A dermoscopy image of a single skin lesion.
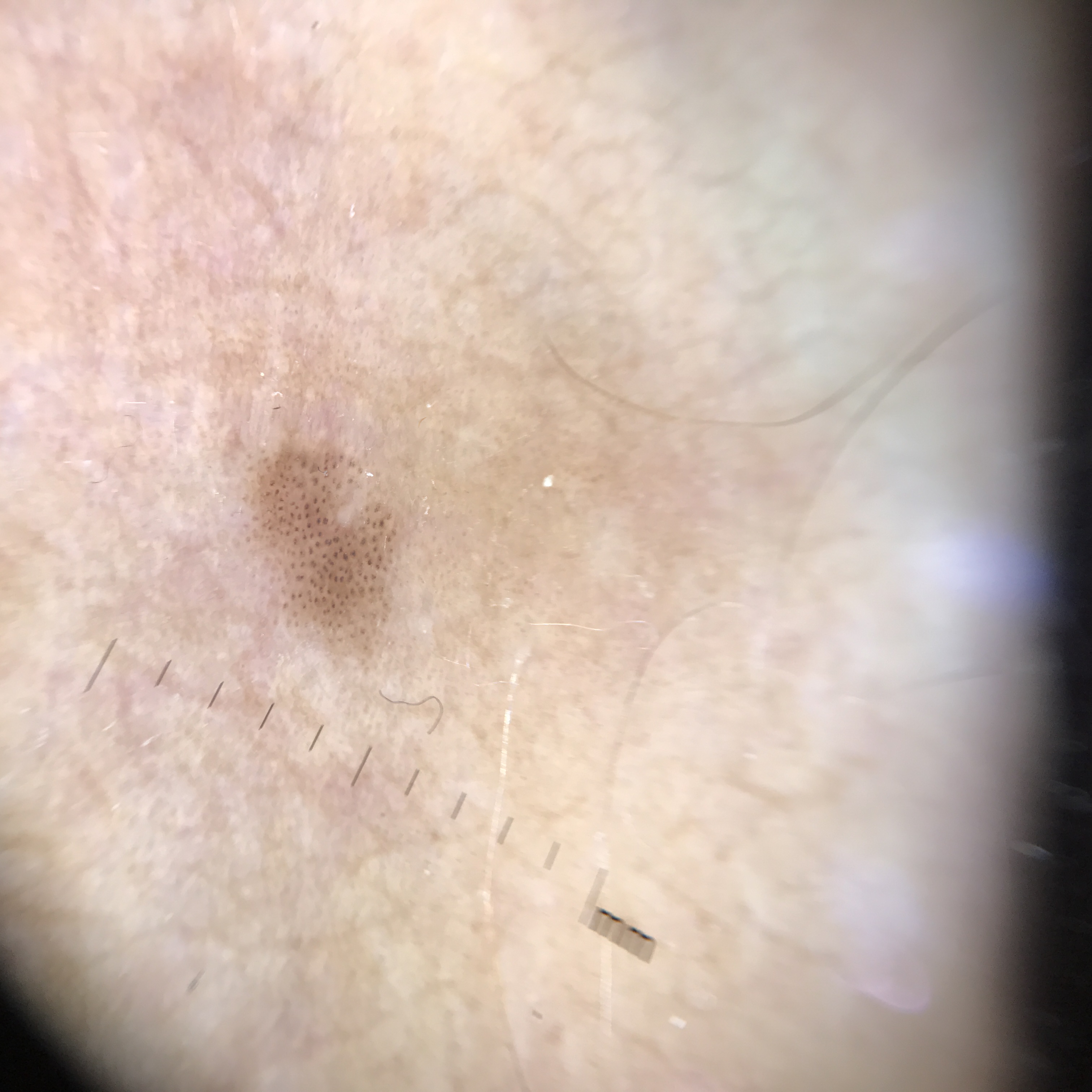The diagnostic label was a banal lesion — a junctional nevus.